Located on the back of the hand; the photo was captured at a distance; the patient is 40–49, male: 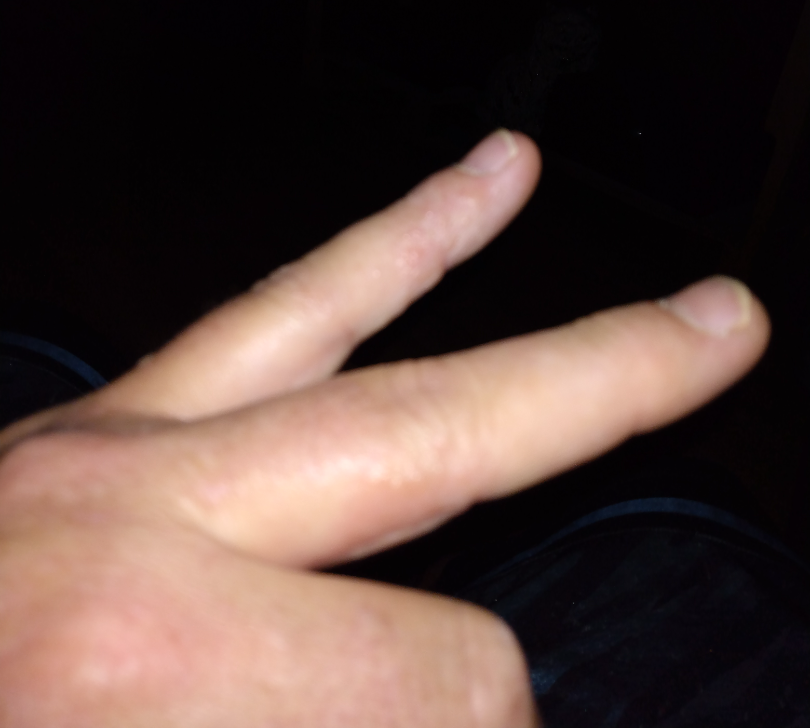Clinical context:
The patient reported no systemic symptoms. The patient reports the lesion is raised or bumpy and fluid-filled. The lesion is associated with itching, pain and enlargement. The patient reports the condition has been present for one to four weeks.
Assessment:
The leading consideration is Eczema; possibly Allergic Contact Dermatitis.